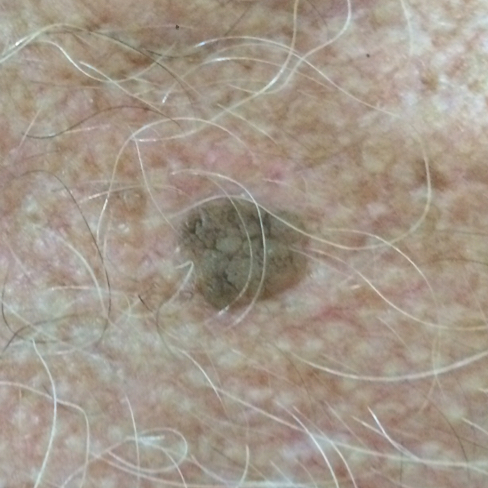A clinical photograph showing a skin lesion. A patient 58 years of age. Located on the chest. The patient reports that the lesion has grown and is elevated. Diagnosed by dermatologist consensus as a seborrheic keratosis.